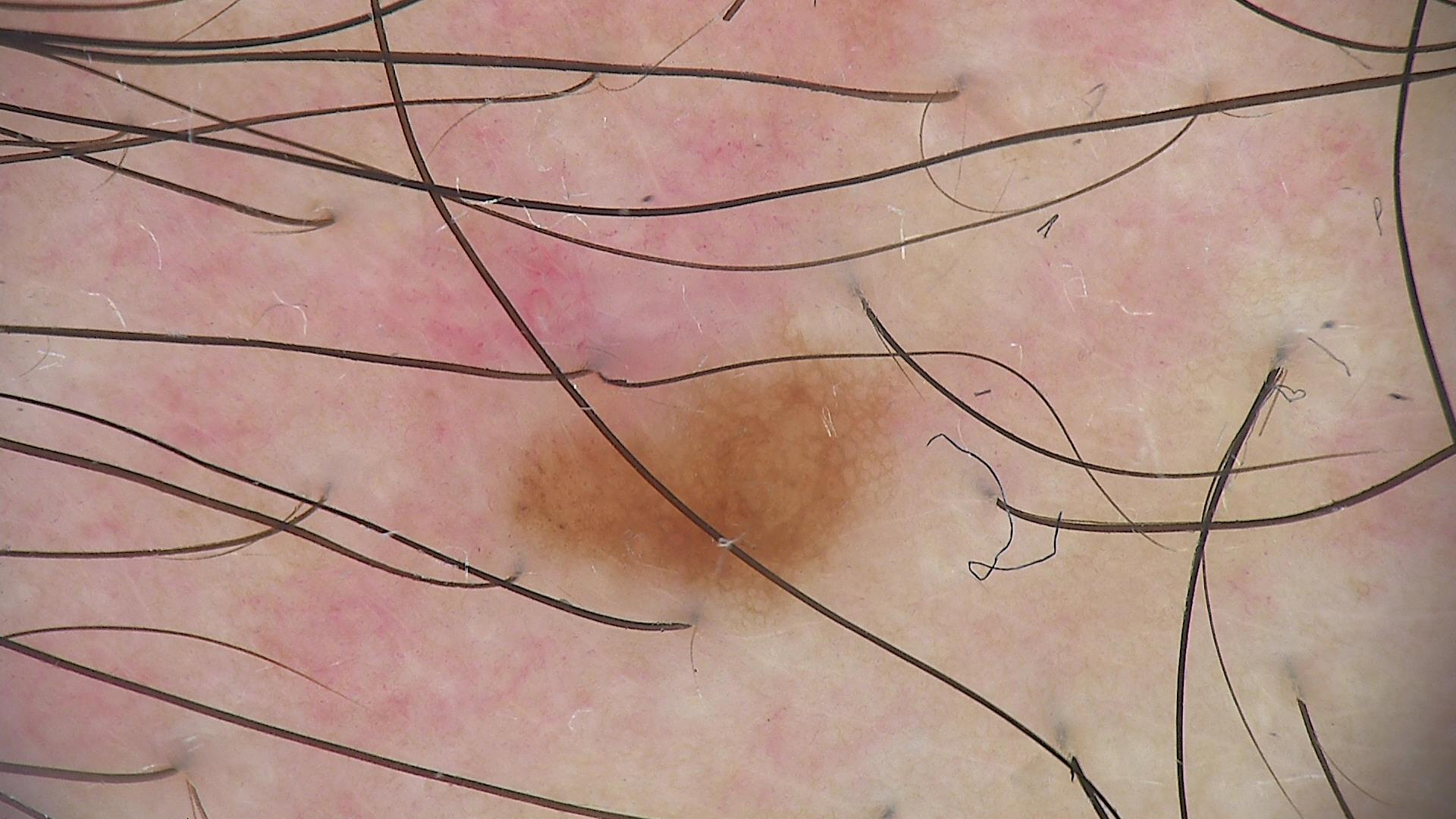modality=dermoscopy | label=dysplastic junctional nevus (expert consensus).